A dermoscopic close-up of a skin lesion · the patient is FST II · a female patient approximately 25 years of age — 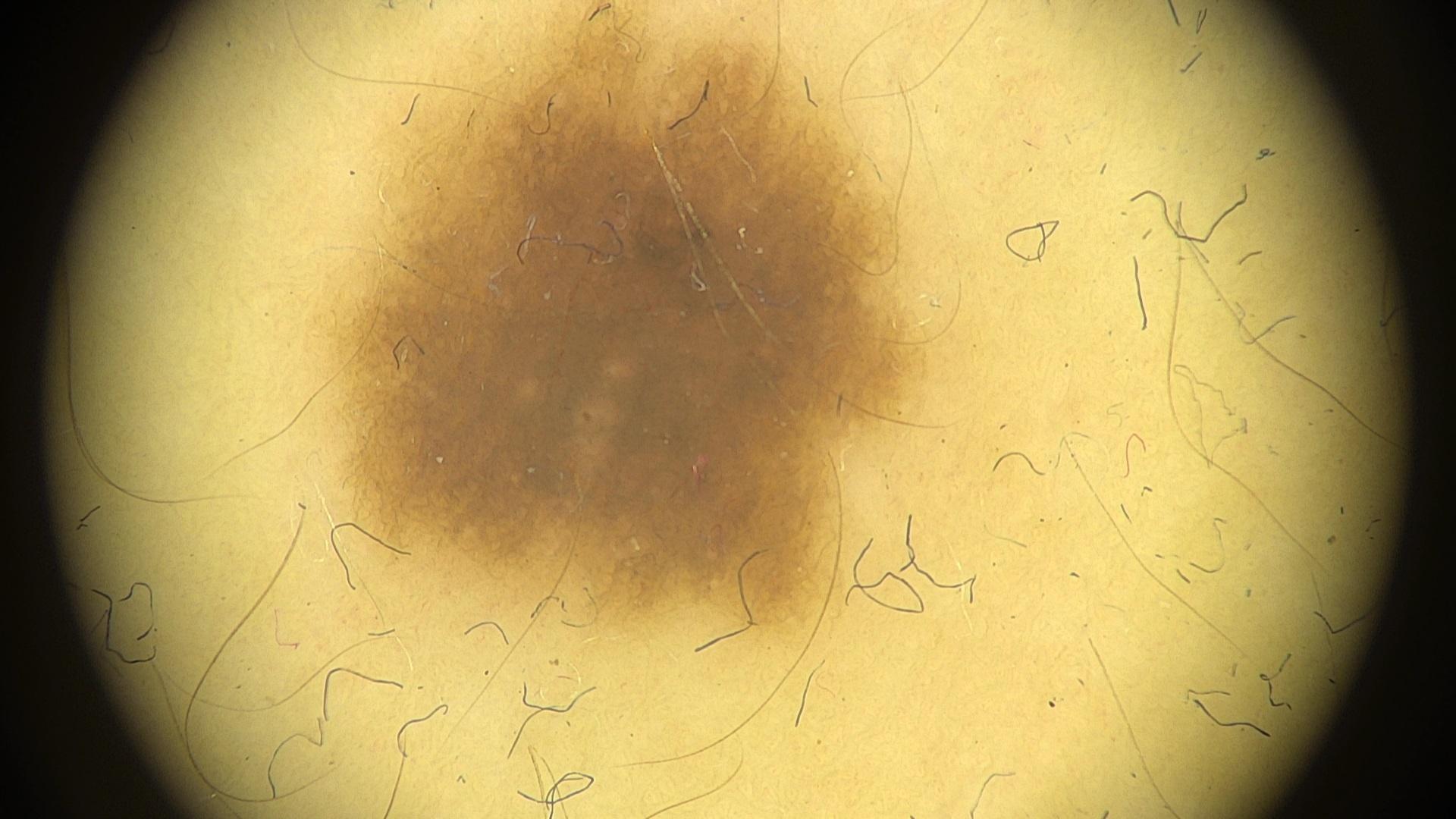The lesion was found on the trunk.
The clinical assessment was a benign lesion — a nevus.